A dermoscopy image of a single skin lesion.
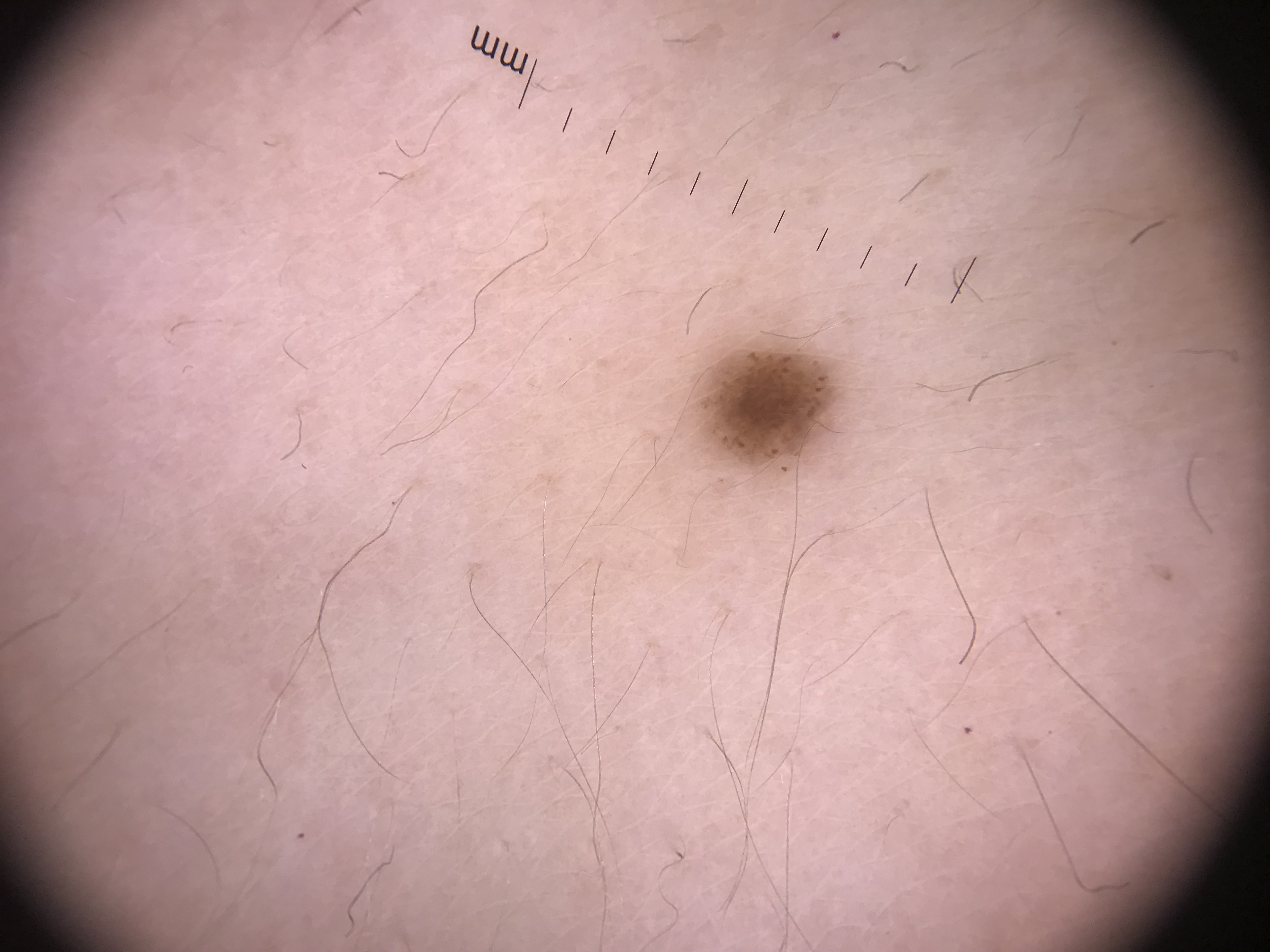Conclusion:
Classified as a banal lesion — a junctional nevus.